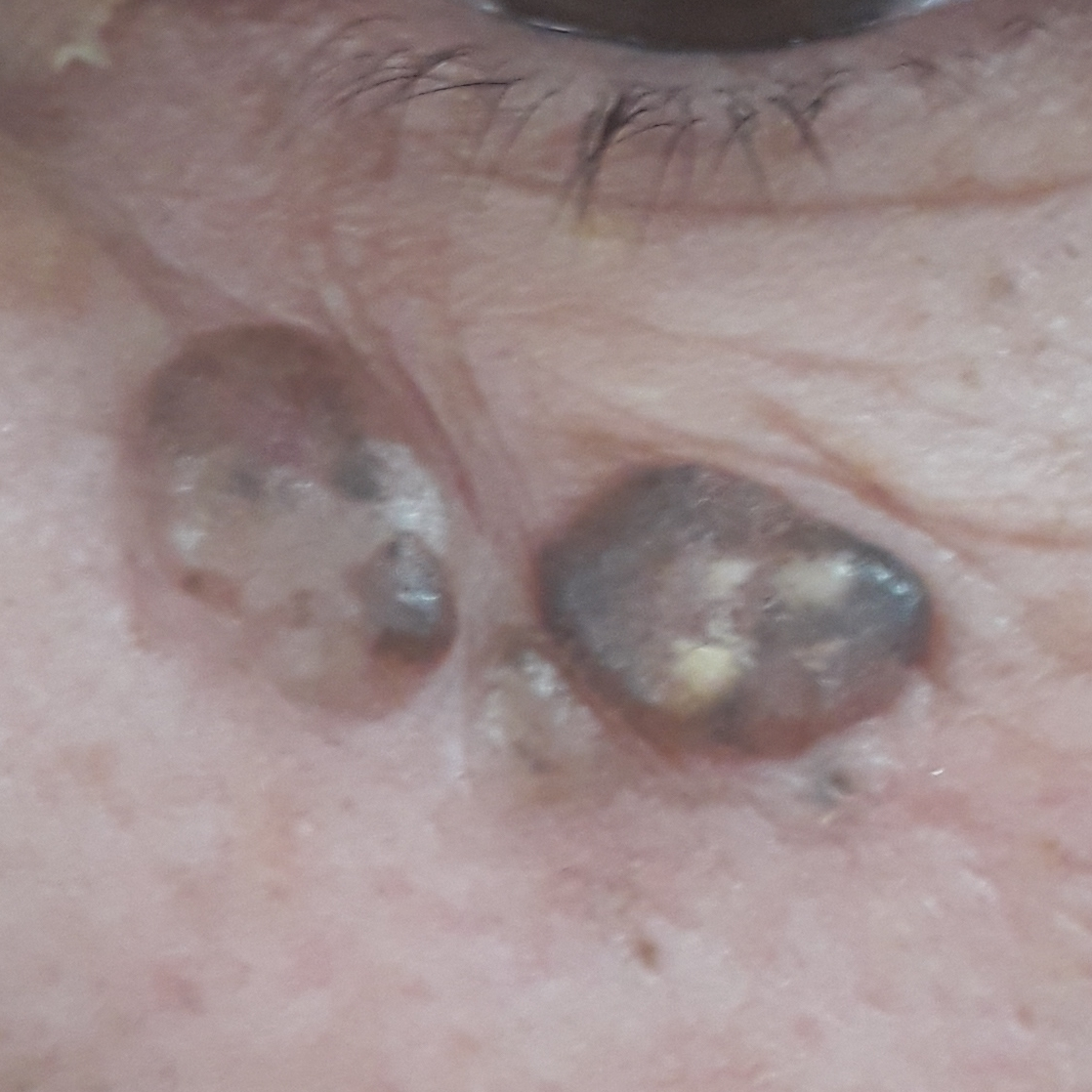diagnosis: basal cell carcinoma (biopsy-proven).